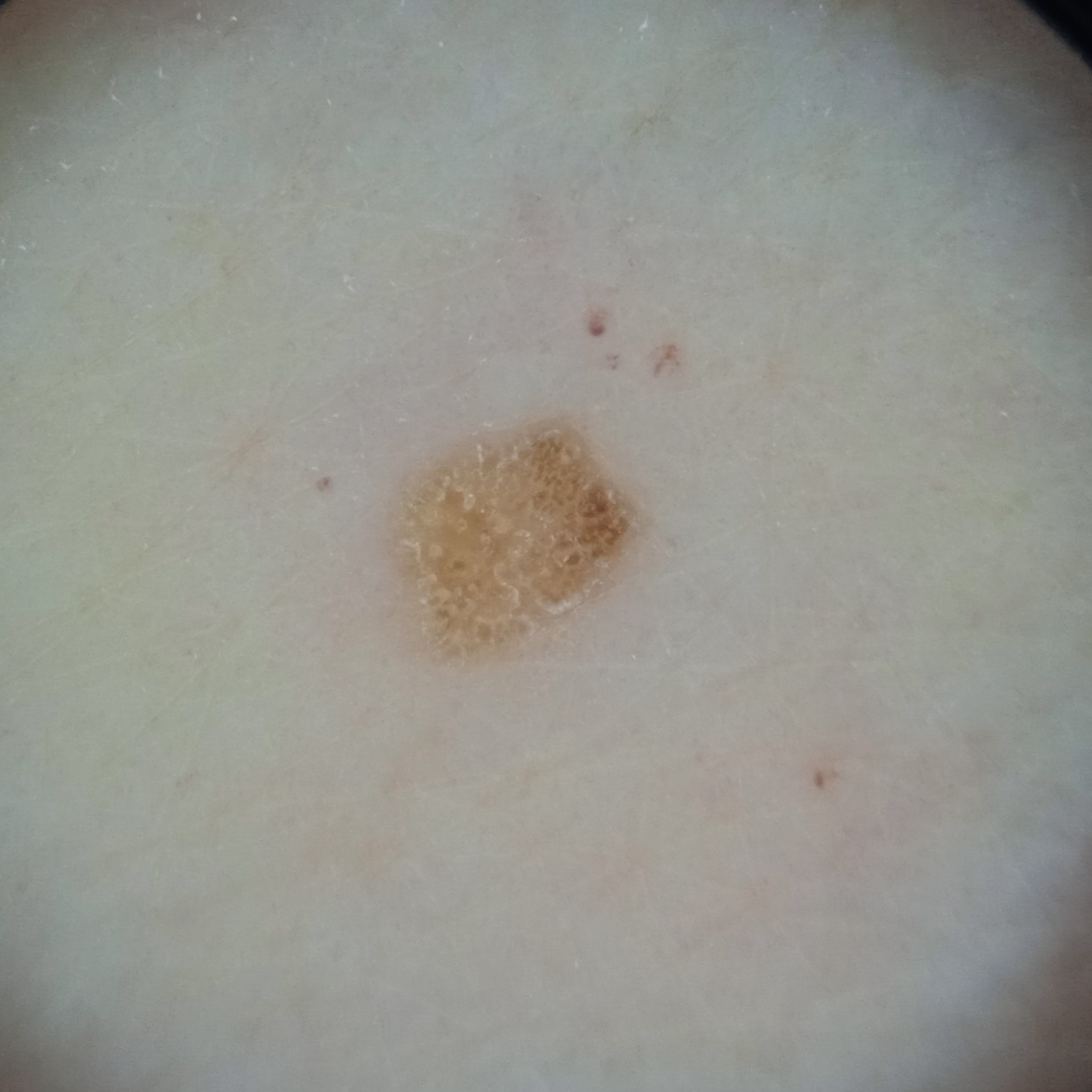Imaged for a research study, with no referral diagnosis recorded.
Few moles overall by the patient's own estimate.
A dermoscopic image of a skin lesion.
A female patient aged 67.
The patient says their skin tans without first burning.
Located on an arm.
The lesion measures approximately 3.1 mm.
The four-dermatologist consensus diagnosis was a seborrheic keratosis; the reviewers were not unanimous.